Associated systemic symptoms include mouth sores. Skin tone: FST II; lay reviewers estimated MST 1 (US pool) or 2 (India pool). The patient described the issue as a rash. The subject is a male aged 18–29. A close-up photograph. The lesion is associated with burning, bleeding and itching. The patient reports the lesion is rough or flaky and fluid-filled. The arm and sole of the foot are involved:
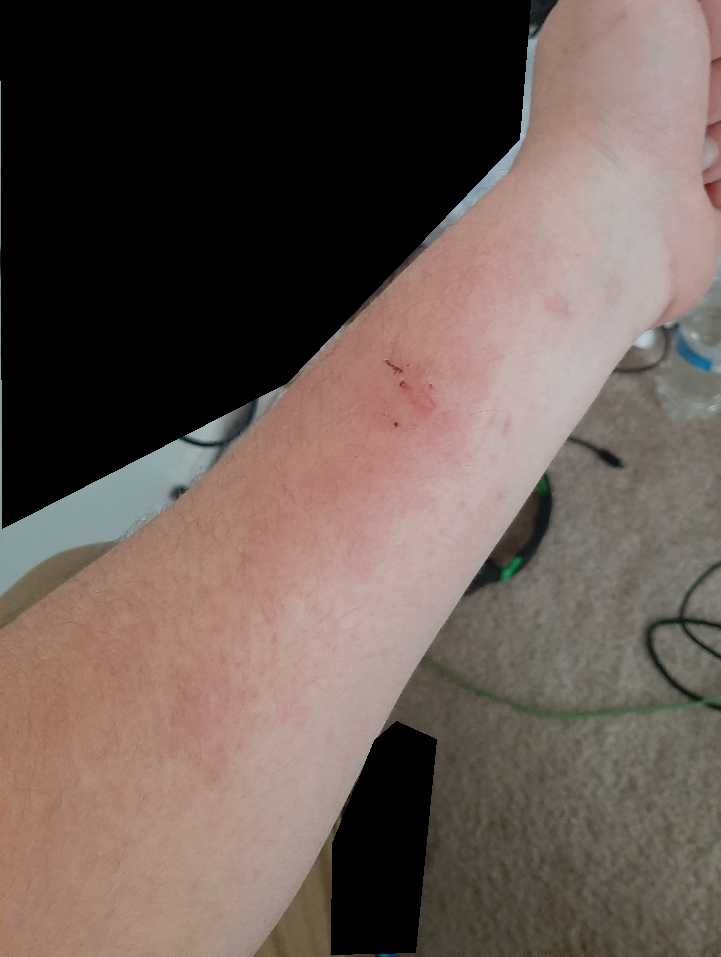Q: What was the assessment?
A: could not be assessed